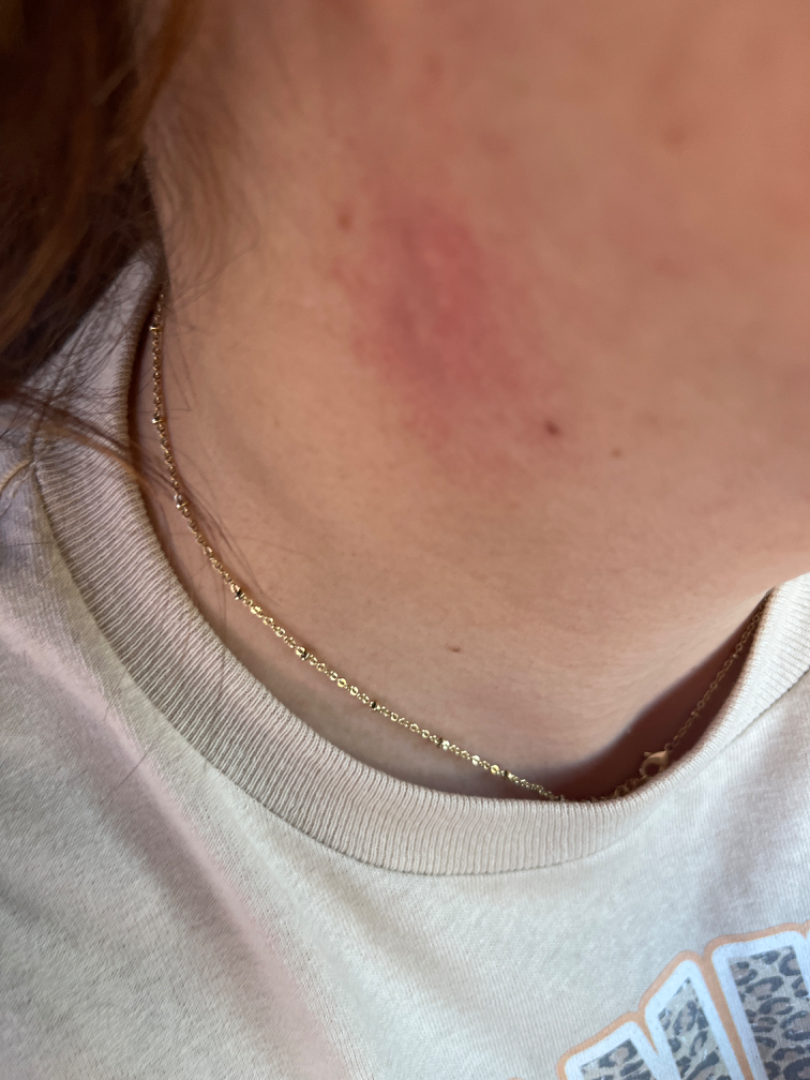Notes:
- location: head or neck
- texture: raised or bumpy
- image framing: at an angle
- onset: less than one week
- skin tone: Fitzpatrick I
- diagnostic considerations: most likely Insect Bite; also consider Acne; possibly Allergic Contact Dermatitis